Acquired for a research image collection, with no referral diagnosis. A female patient age 75. A dermoscopy image of a skin lesion:
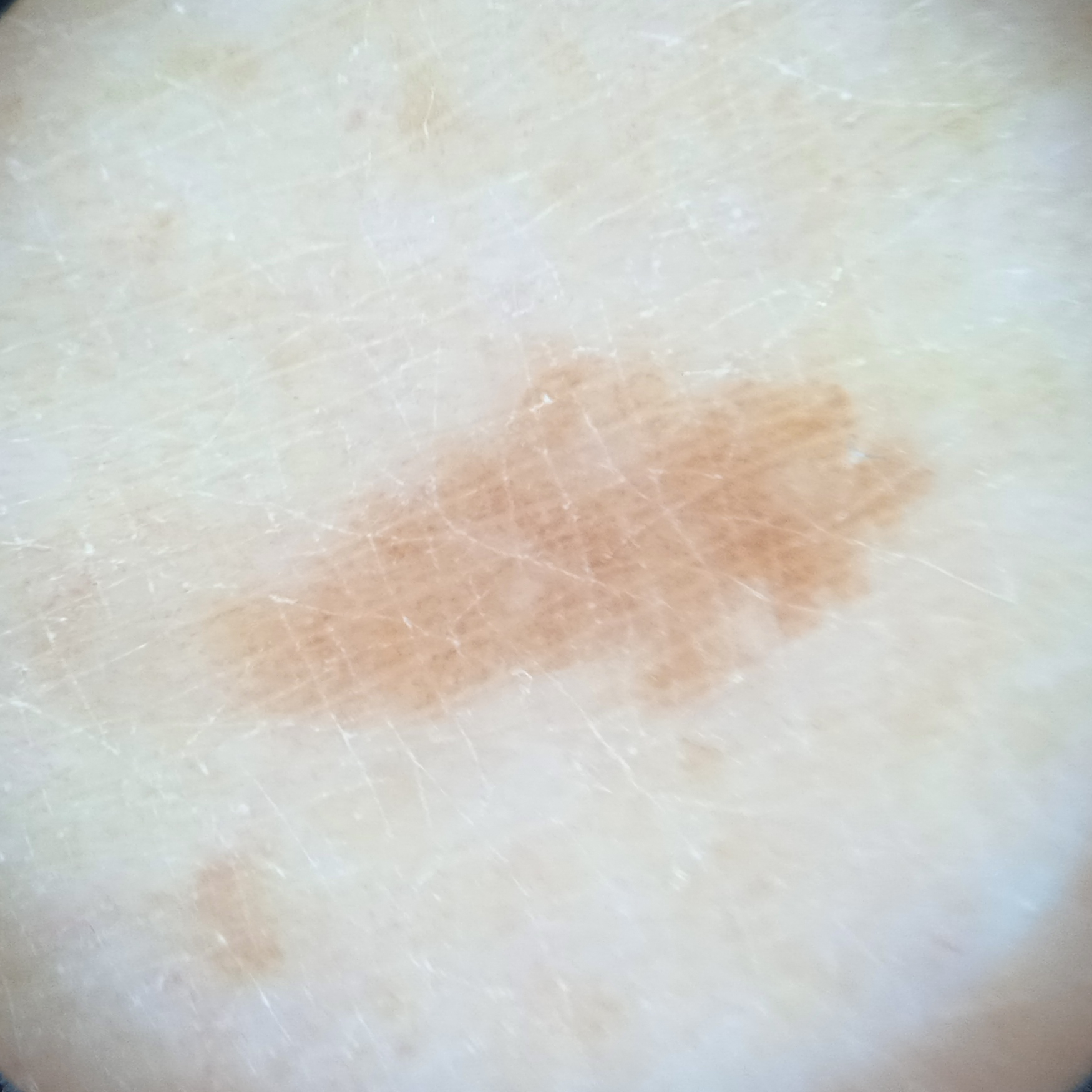<skin_lesion>
  <lesion_location>a leg</lesion_location>
  <lesion_size>
    <diameter_mm>8.2</diameter_mm>
  </lesion_size>
  <diagnosis>
    <name>melanocytic nevus</name>
    <malignancy>benign</malignancy>
  </diagnosis>
</skin_lesion>